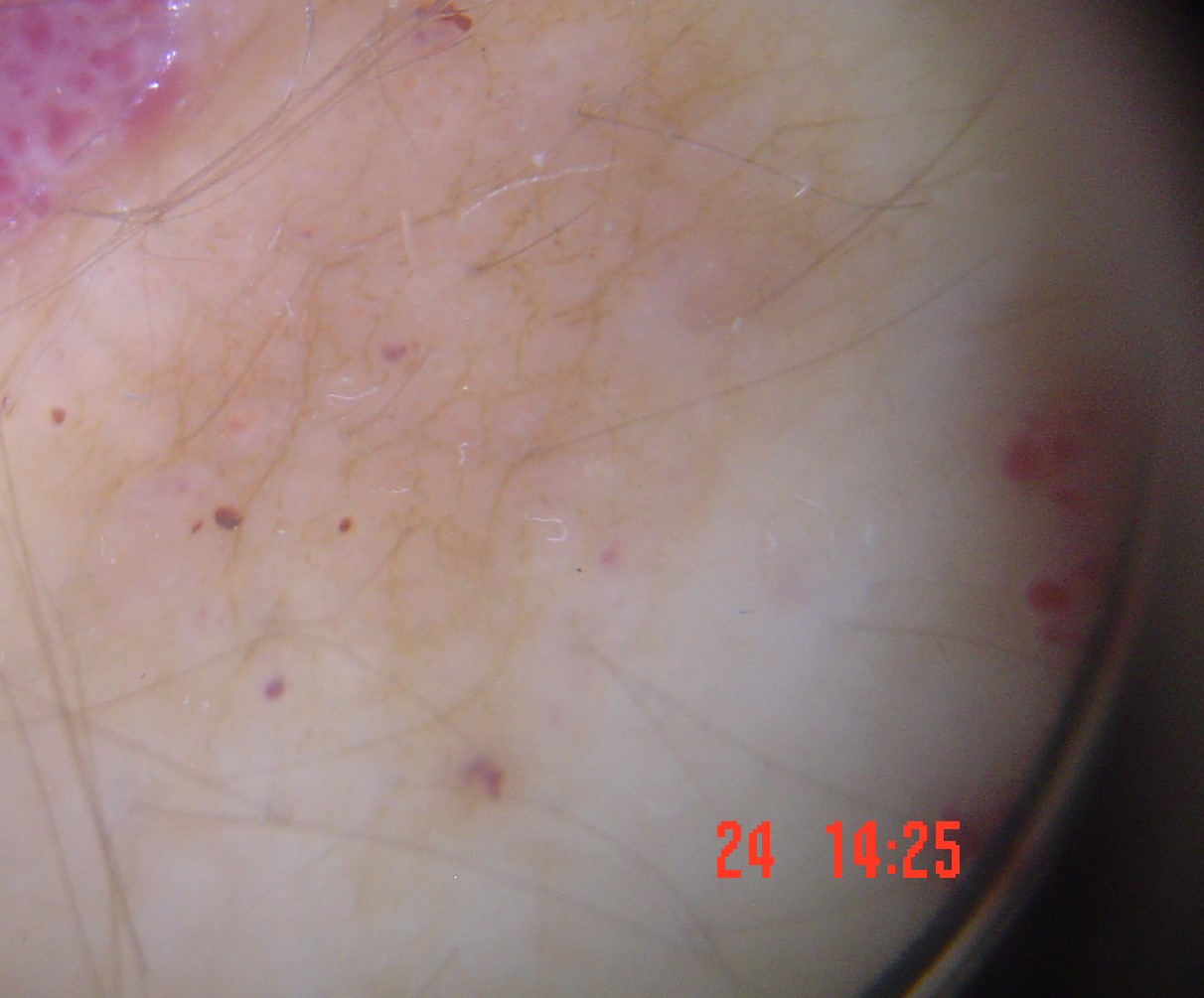The architecture is that of a vascular lesion. The diagnosis was a benign lesion — a lymphangioma.